The chart notes prior skin cancer (patient or family), prior malignancy (patient or family), and pesticide exposure — 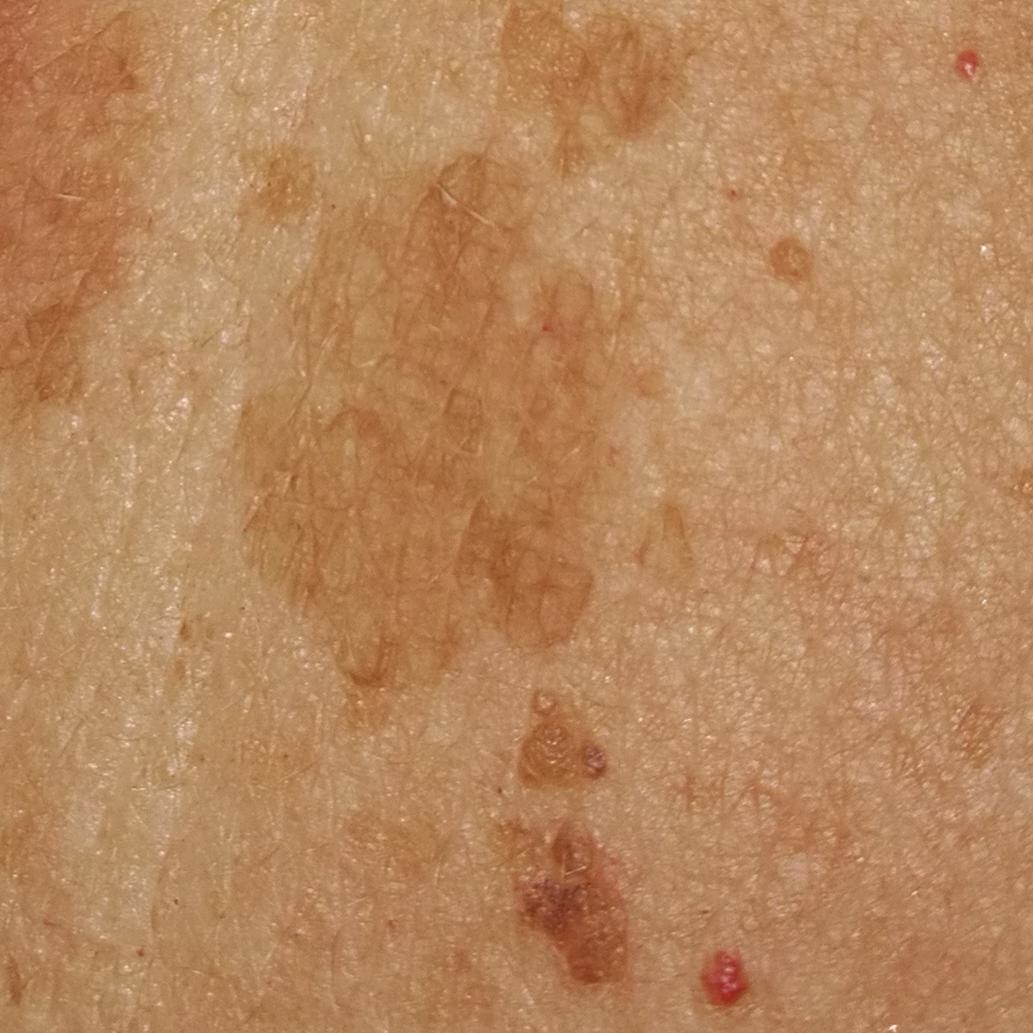The lesion is on the back.
The lesion measures 3 × 3 mm.
By the patient's account, the lesion itches, is elevated, and has grown.
Consistent with a benign skin lesion — a seborrheic keratosis.